A dermatoscopic image of a skin lesion. A male subject aged 65. Imaged for a research study, with no referral diagnosis recorded: 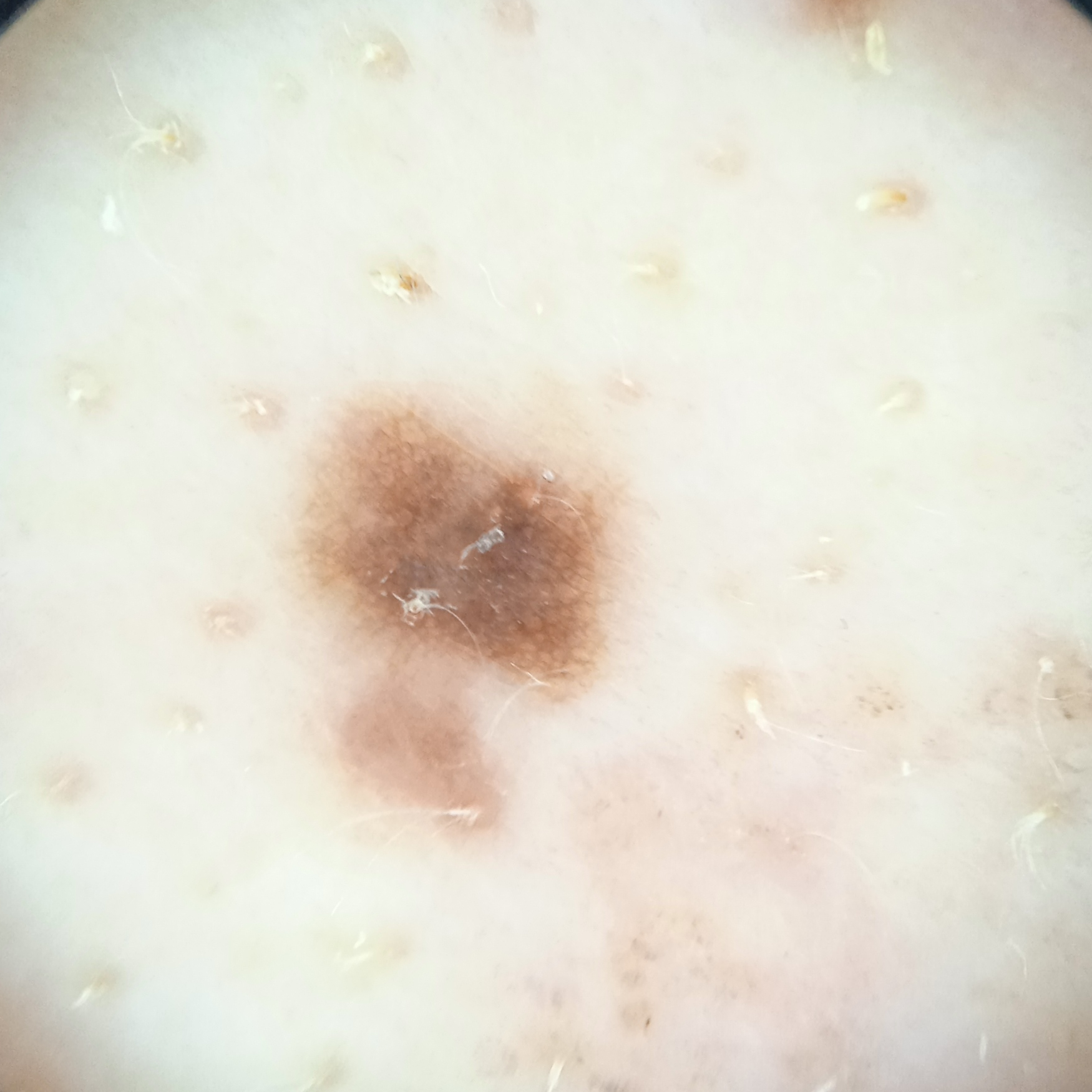{"lesion_size": {"diameter_mm": 4.2}, "diagnosis": {"name": "atypical (dysplastic) nevus", "malignancy": "benign", "unanimous": false, "certainty": "moderate"}}